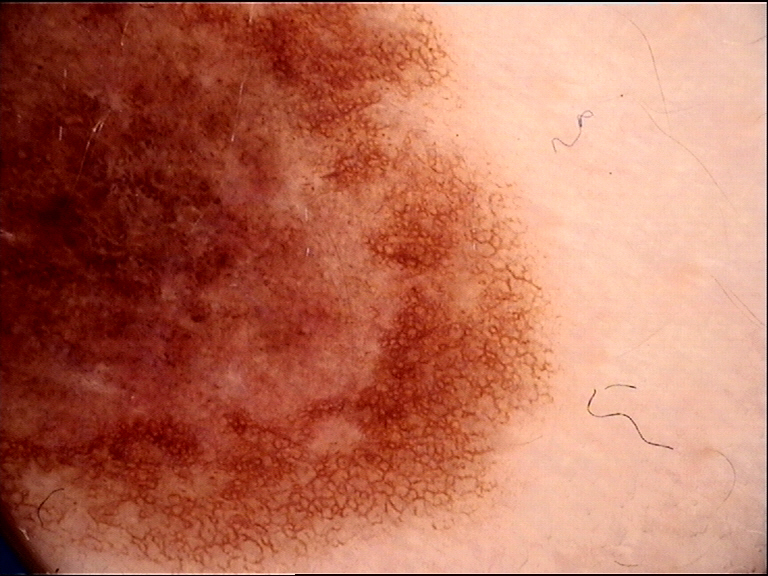The diagnostic label was a congenital dysplastic compound nevus.